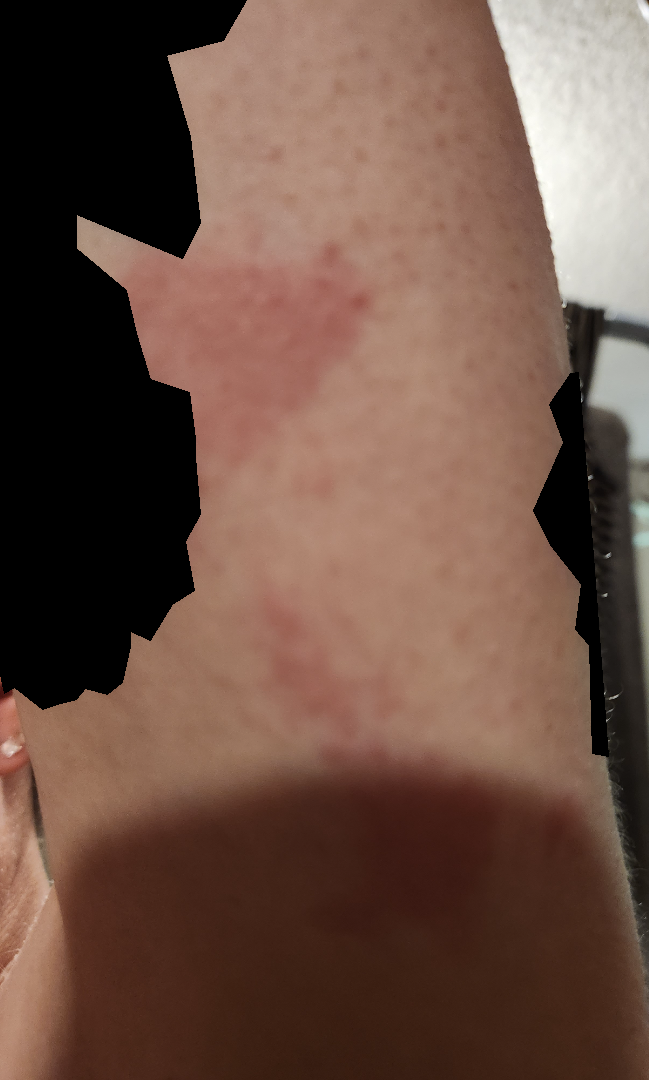{"assessment": "ungradable on photographic review", "duration": "about one day", "symptoms": "itching", "texture": ["raised or bumpy", "flat"], "skin_tone": {"fitzpatrick": "II", "monk_skin_tone": [2, 3]}, "body_site": "arm", "shot_type": "close-up"}